A dermatoscopic image of a skin lesion.
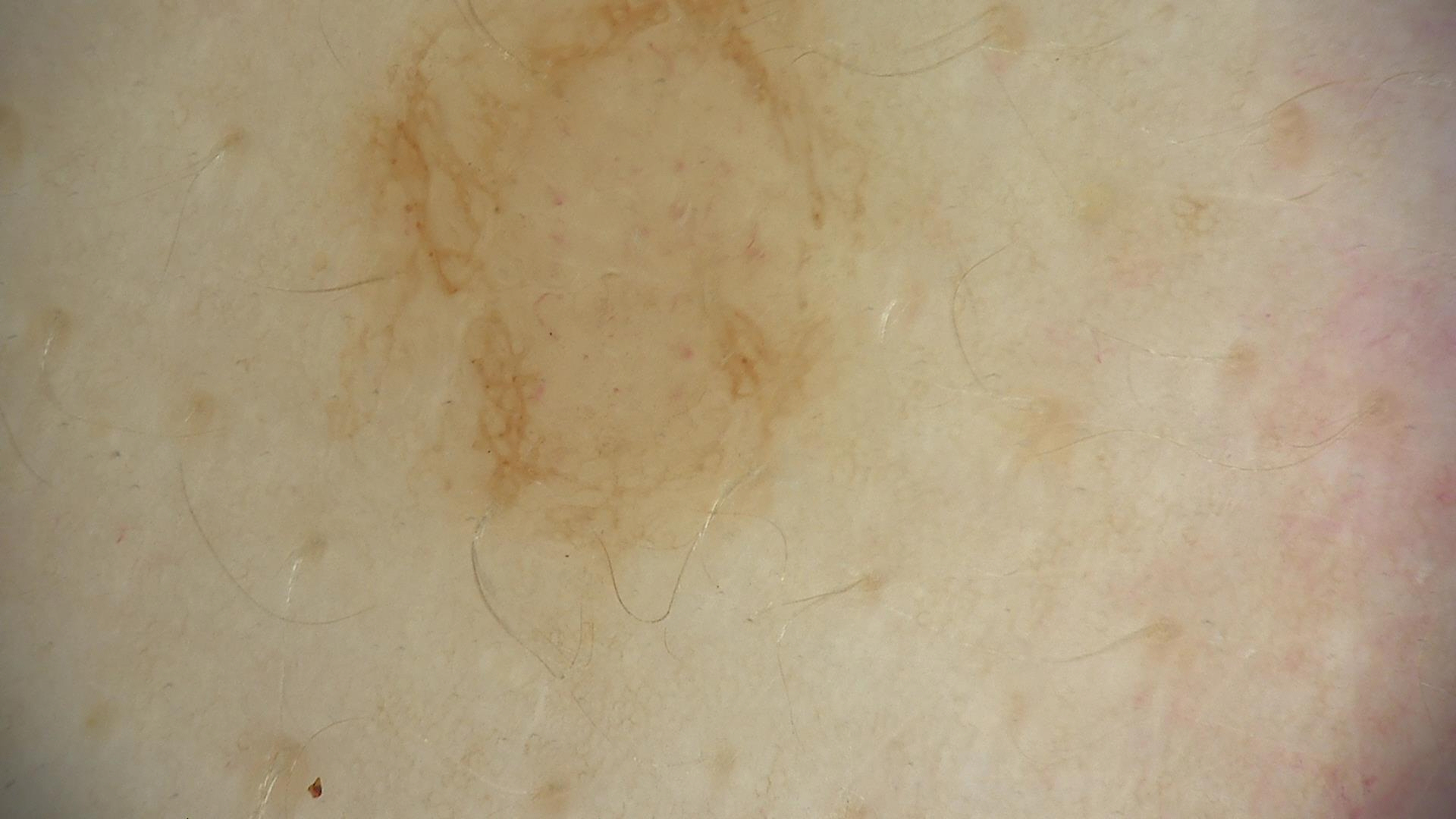Findings:
* class: dysplastic junctional nevus (expert consensus)